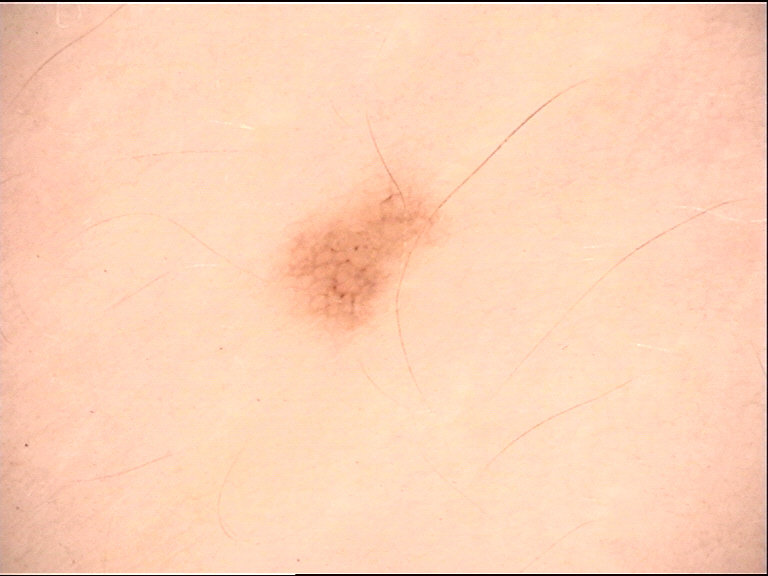label = dysplastic junctional nevus (expert consensus)